Close-up view: 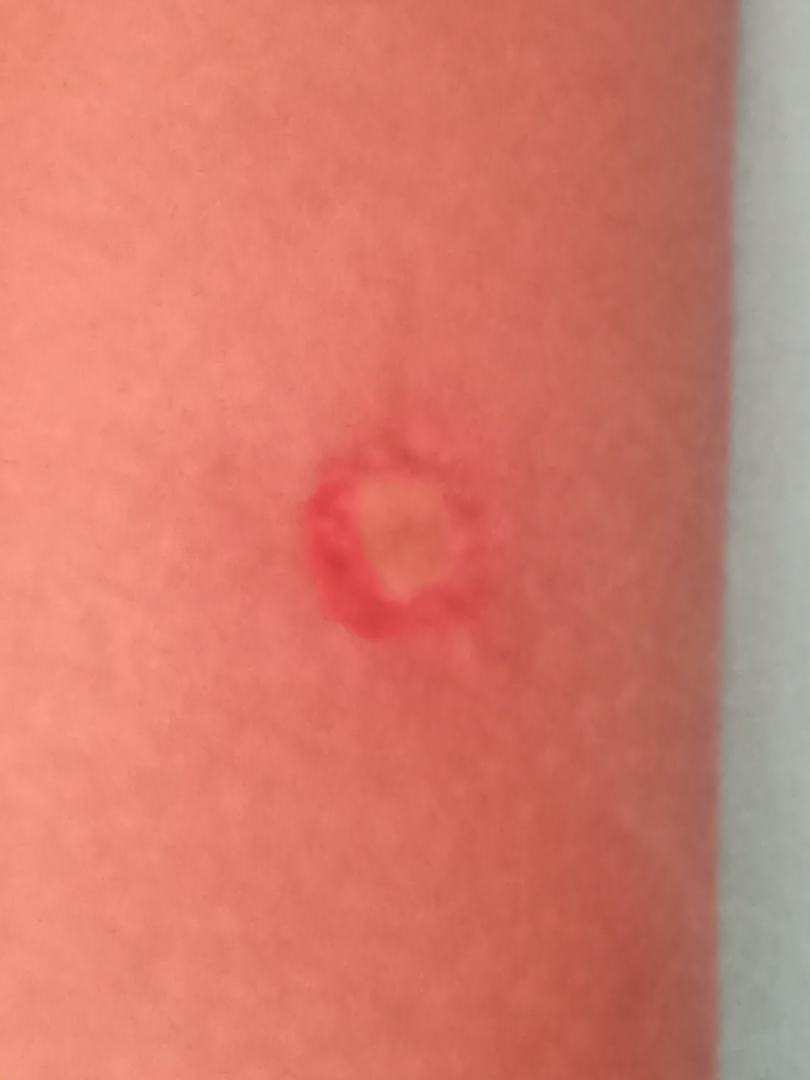Assessment:
No differential diagnosis could be assigned on photographic review.